This image was taken at an angle · the lesion involves the arm, front of the torso, head or neck and leg · the patient described the issue as a rash · texture is reported as flat · symptoms reported: itching and bleeding · no constitutional symptoms were reported · skin tone: FST II; lay graders estimated Monk Skin Tone 2 or 3 · the condition has been present for less than one week · the contributor is 18–29, female.
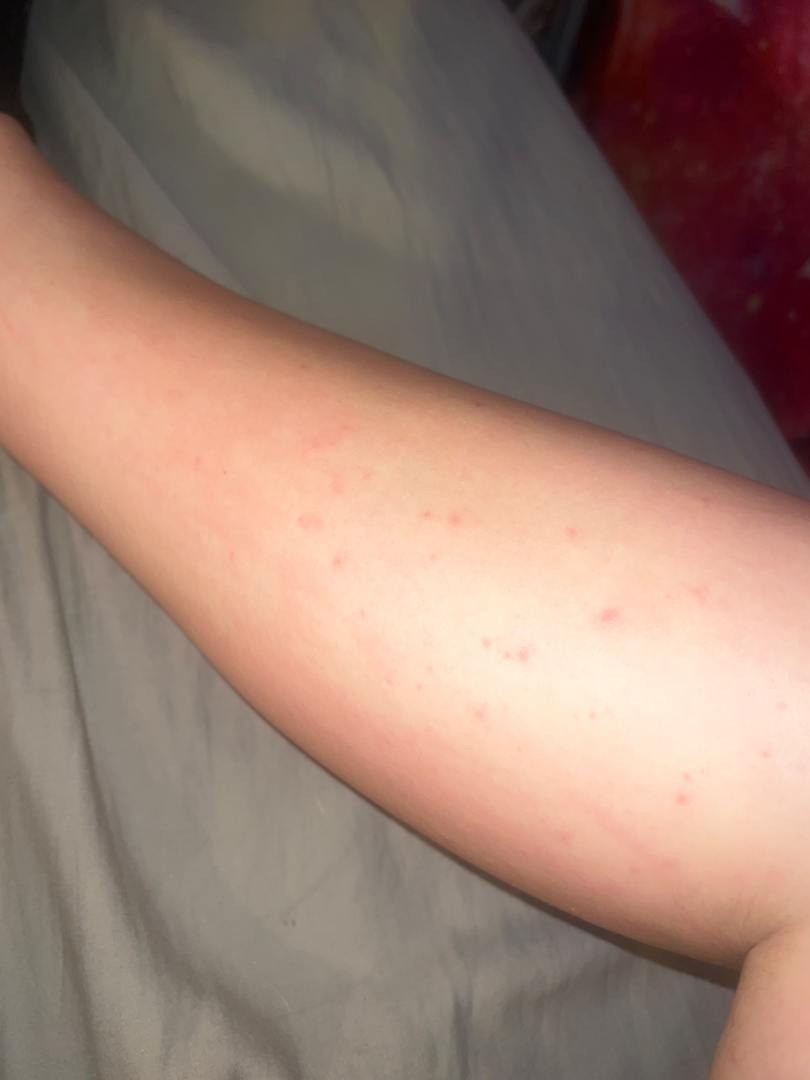diagnostic considerations = three dermatologists each reviewed the case: most likely Insect Bite; an alternative is Eczema; the differential also includes Molluscum Contagiosum; less likely is Allergic Contact Dermatitis; less probable is Abrasion, scrape, or scab